The patient says their skin reddens with sun exposure; a moderate number of moles by the patient's own estimate.
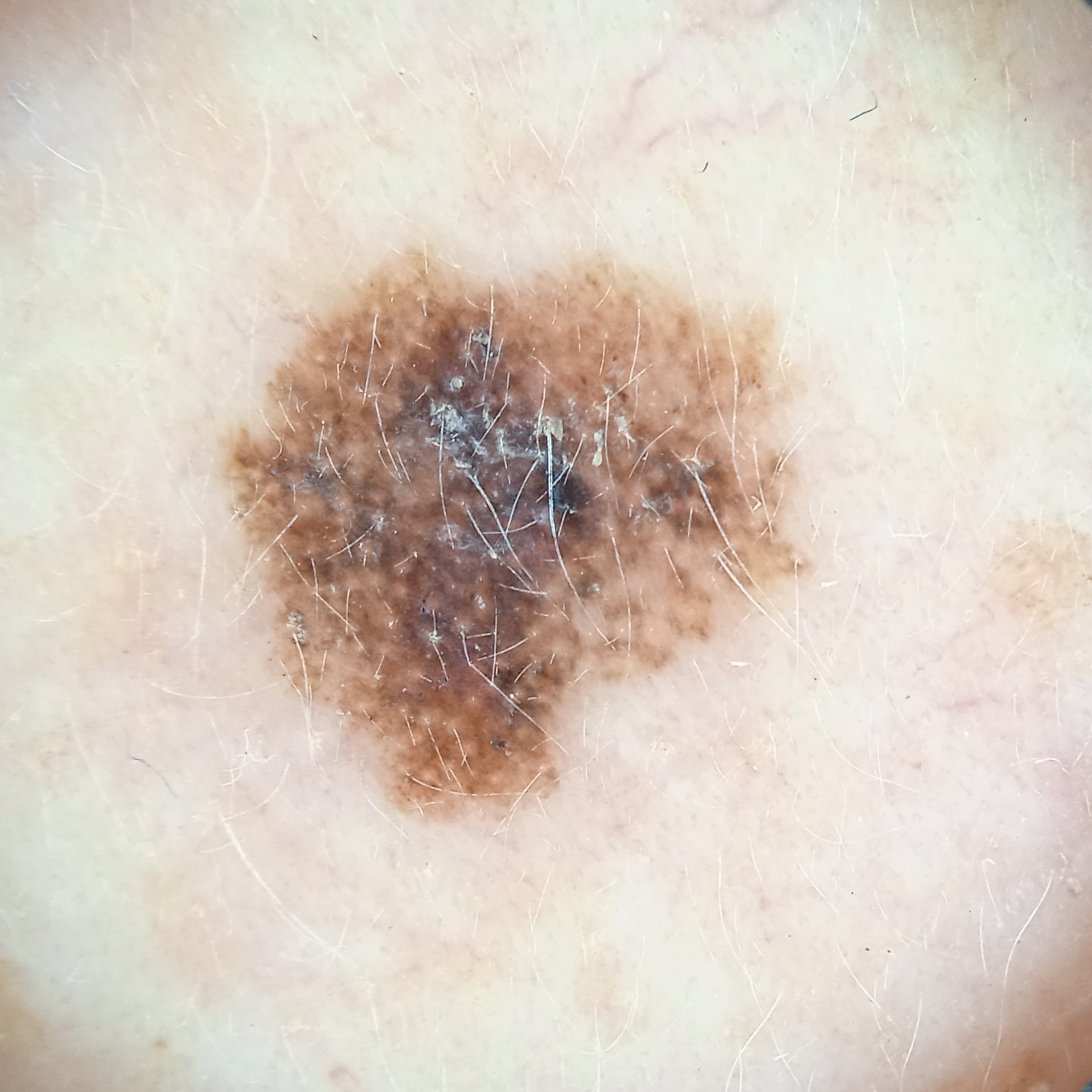body site: the face, size: 7 mm, pathology: melanoma (biopsy-proven).